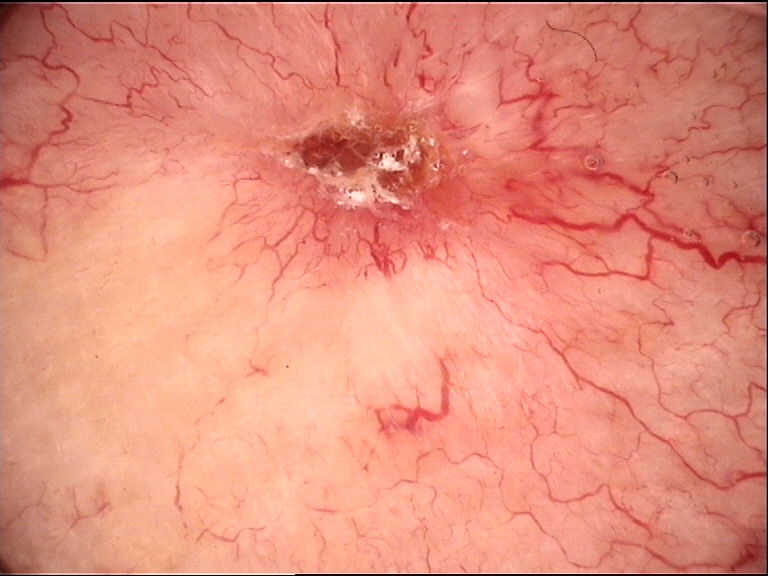Conclusion: Histopathologically confirmed as a basal cell carcinoma.